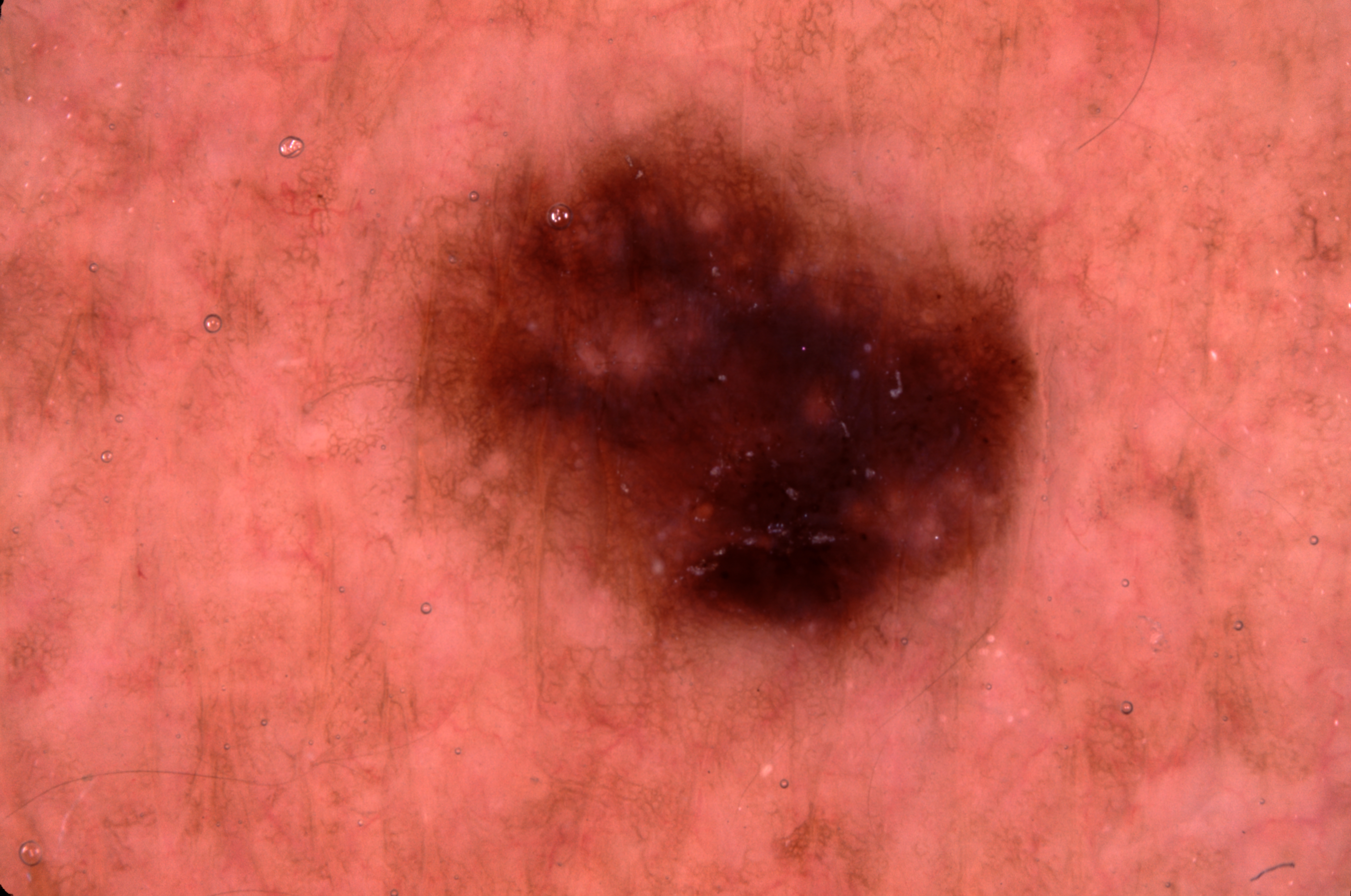Summary: A male patient. A dermoscopy image of a single skin lesion. The lesion covers approximately 20% of the dermoscopic field. On dermoscopy, the lesion shows pigment network and milia-like cysts, with no negative network or streaks. As (left, top, right, bottom), the lesion is bounded by <box>412, 119, 1034, 658</box>. Assessment: Expert review diagnosed this as a melanocytic nevus.